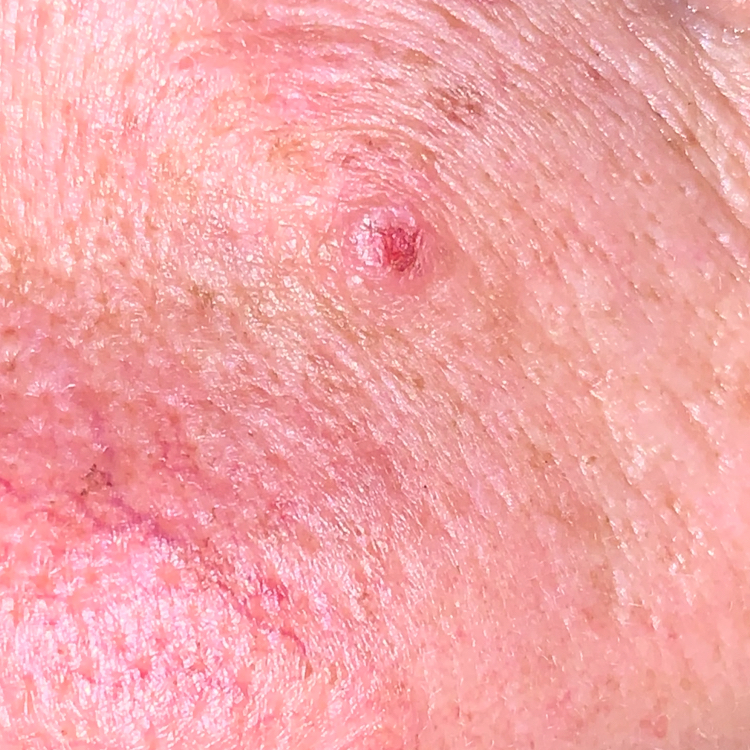Histopathologically confirmed as a basal cell carcinoma.